A dermoscopy image of a single skin lesion.
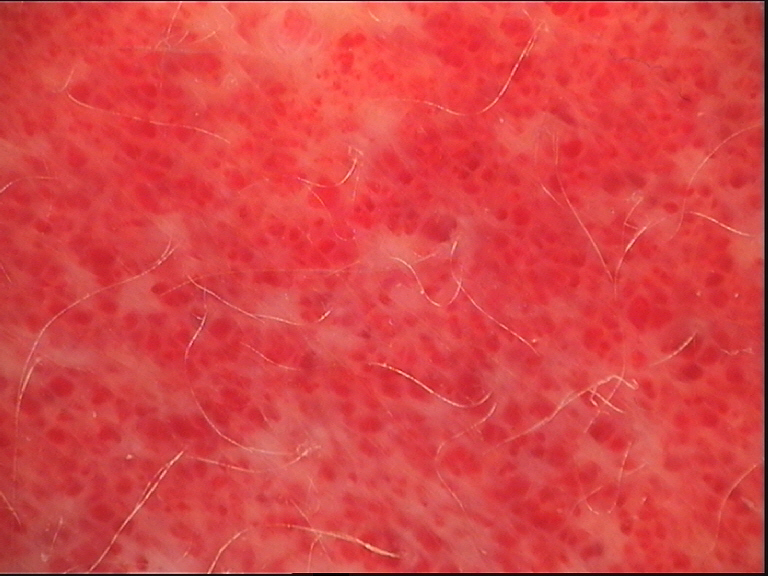label: hemangioma (expert consensus)